The contributor is a male aged 60–69, the lesion involves the leg, a close-up photograph: 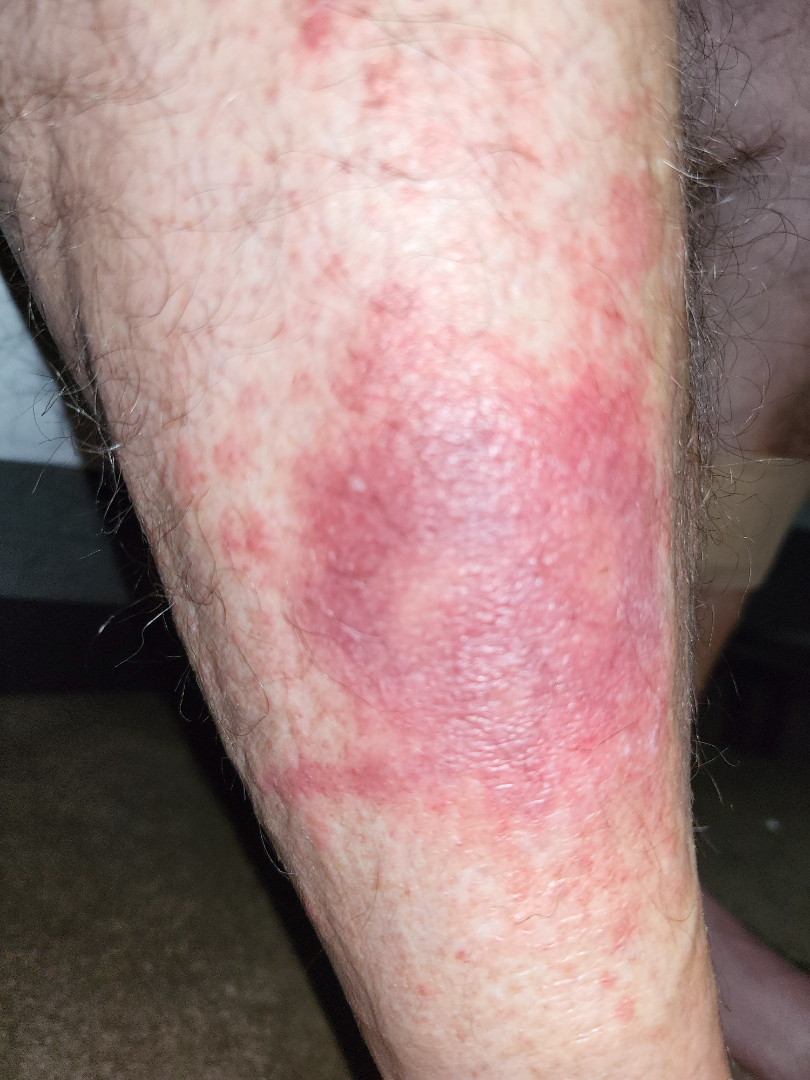A single dermatologist reviewed the case: most likely Allergic Contact Dermatitis; possibly Eczema; an alternative is Stasis Dermatitis.